Per the chart, a previous melanoma but no first-degree relative with melanoma; the patient was assessed as Fitzpatrick II: 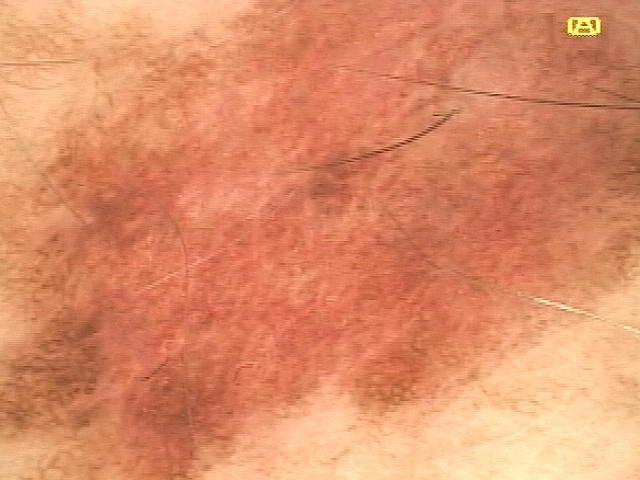<record>
<lesion_location>
<region>the trunk</region>
<detail>the posterior trunk</detail>
</lesion_location>
<diagnosis>
<name>Melanoma</name>
<malignancy>malignant</malignancy>
<confirmation>histopathology</confirmation>
</diagnosis>
</record>